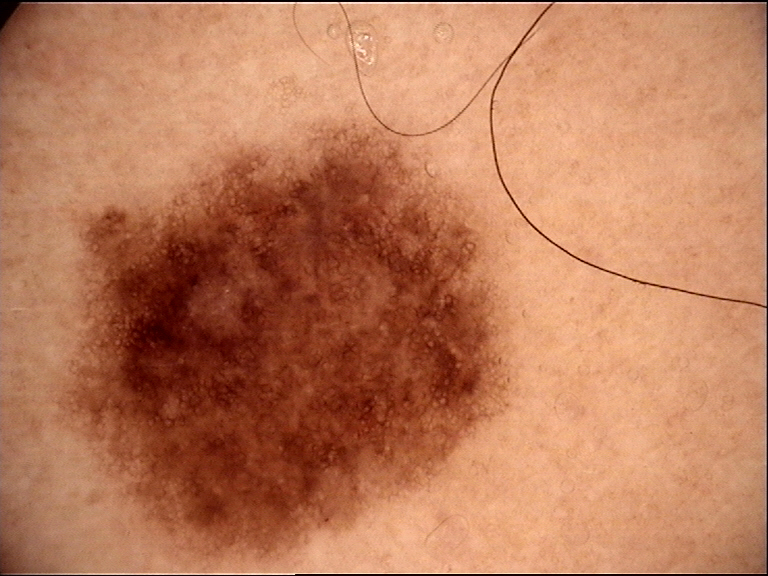Diagnosed as a benign lesion — a dysplastic junctional nevus.